A dermatoscopic image of a skin lesion.
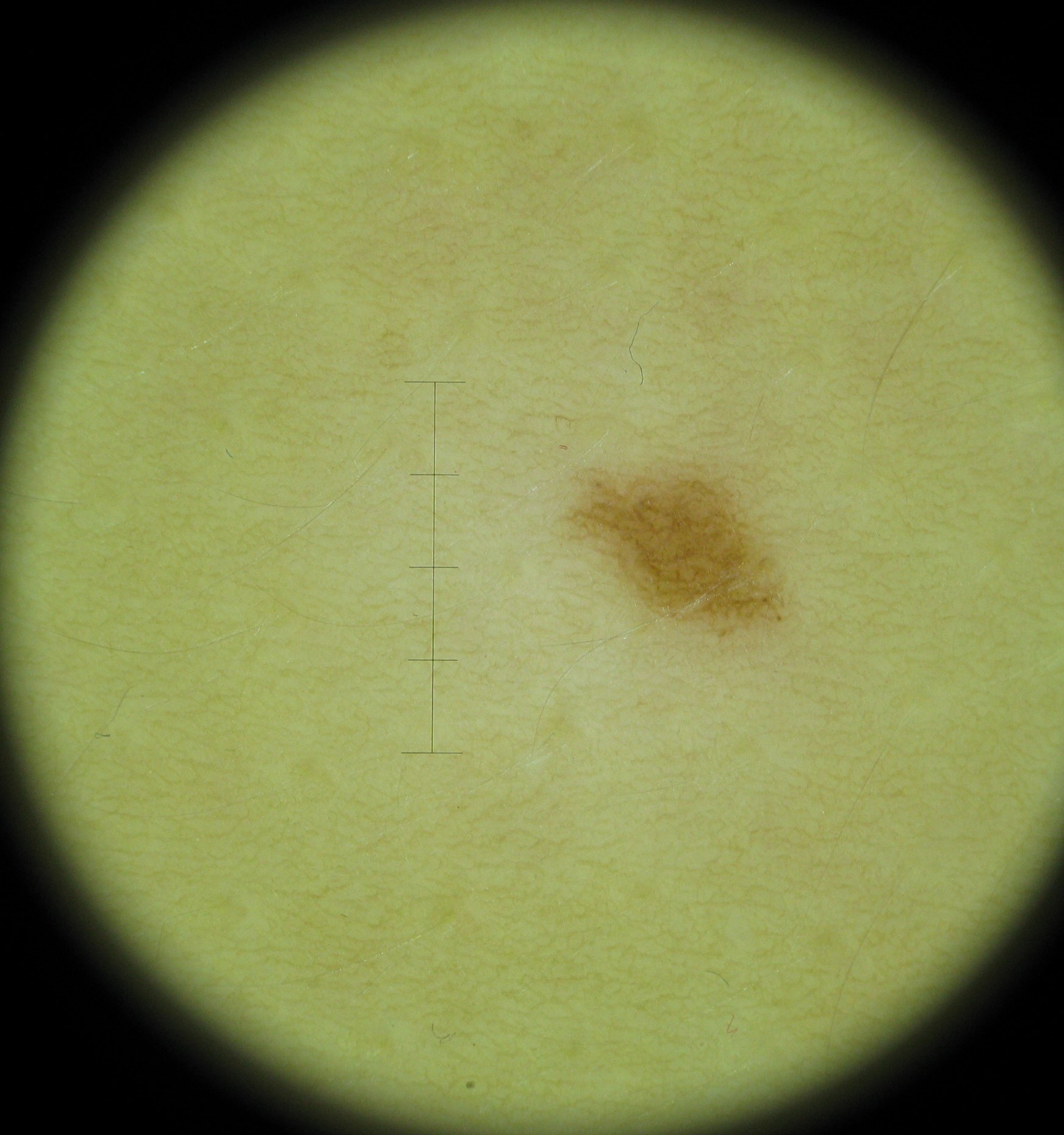The architecture is that of a banal lesion. Classified as a junctional nevus.